This image was taken at an angle; the subject is 60–69, female; reported duration is less than one week; the front of the torso, head or neck and arm are involved; associated systemic symptoms include shortness of breath; the lesion is associated with itching, burning and bothersome appearance — 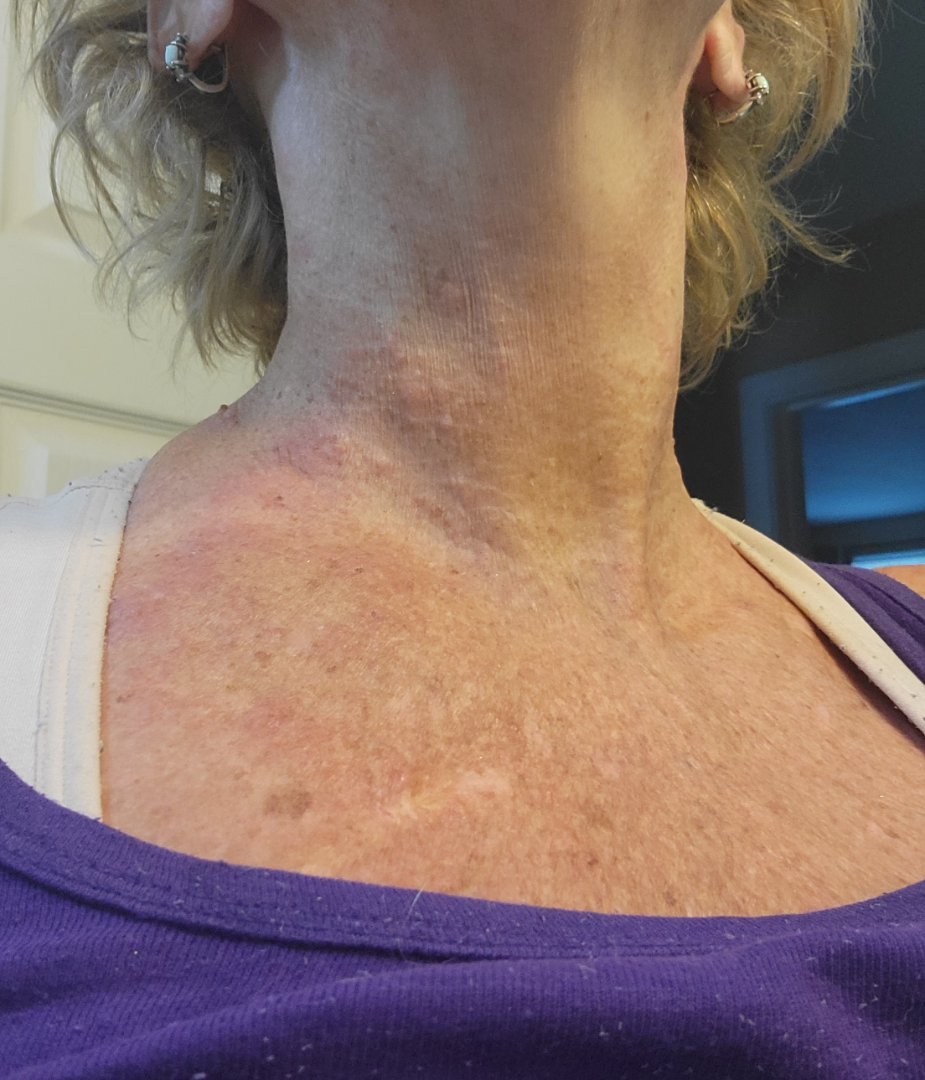Impression:
The reviewing dermatologist was unable to assign a differential diagnosis from the image.